A patient aged 62 — 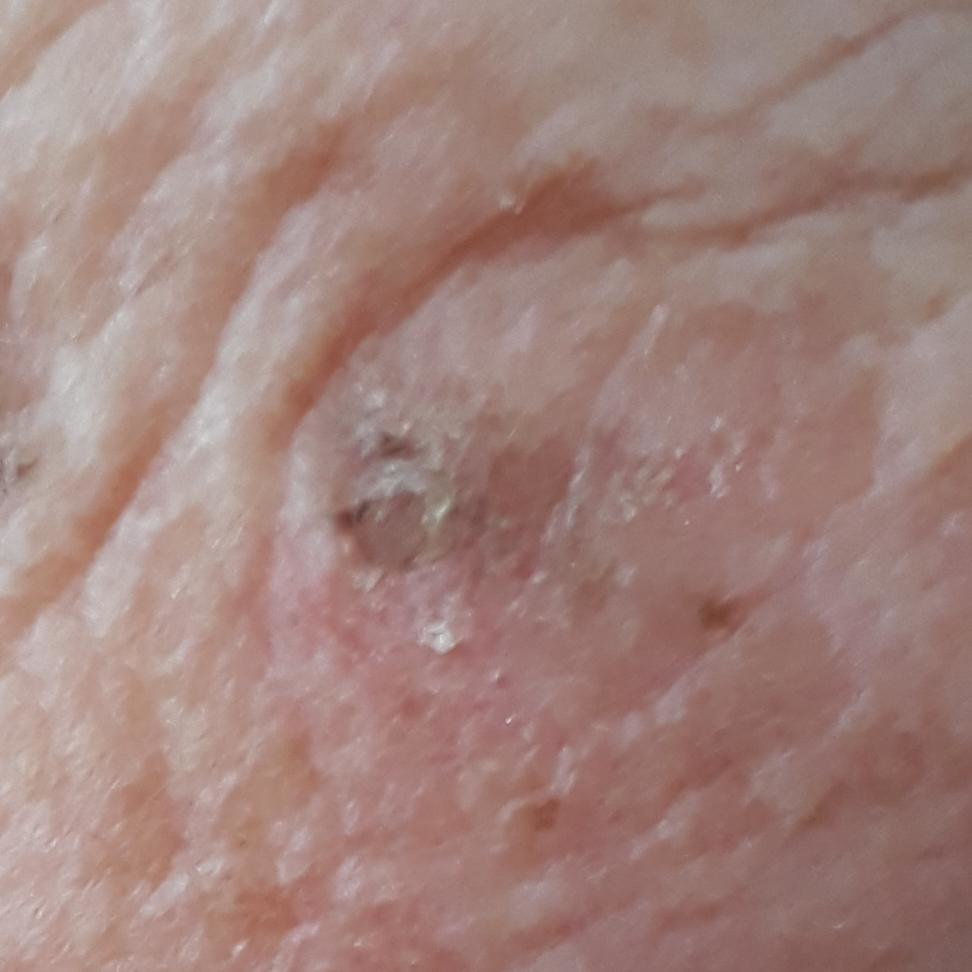body site = the face
reported symptoms = growth, elevation
assessment = seborrheic keratosis (clinical consensus)